A subject 22 years of age:
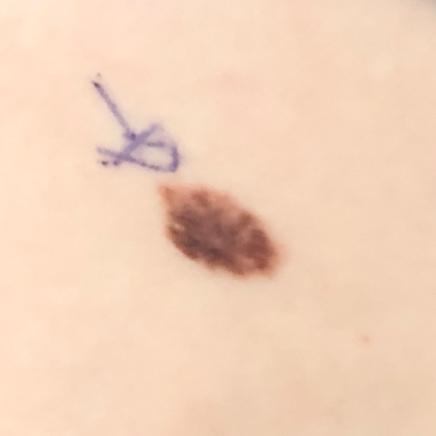Case summary:
The lesion was found on the chest. Asymptomatic by report.
Conclusion:
Clinically diagnosed as a nevus.